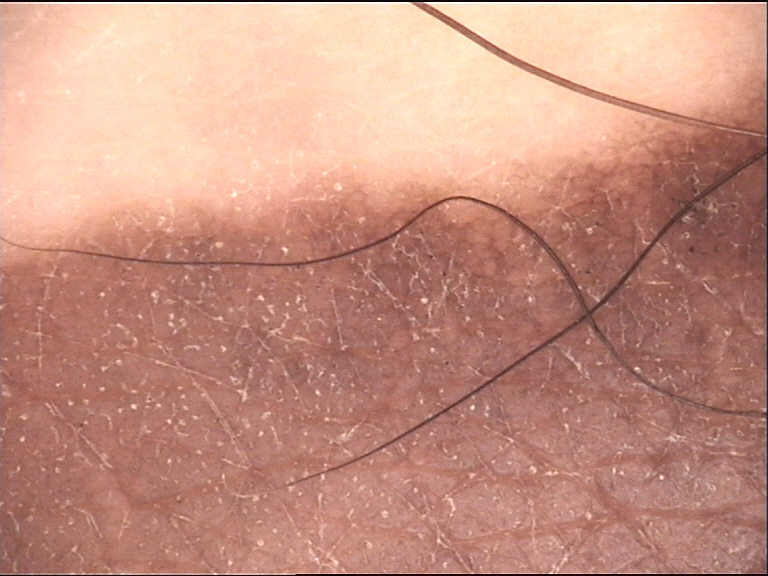diagnosis:
  name: congenital compound nevus
  code: ccb
  malignancy: benign
  super_class: melanocytic
  confirmation: expert consensus